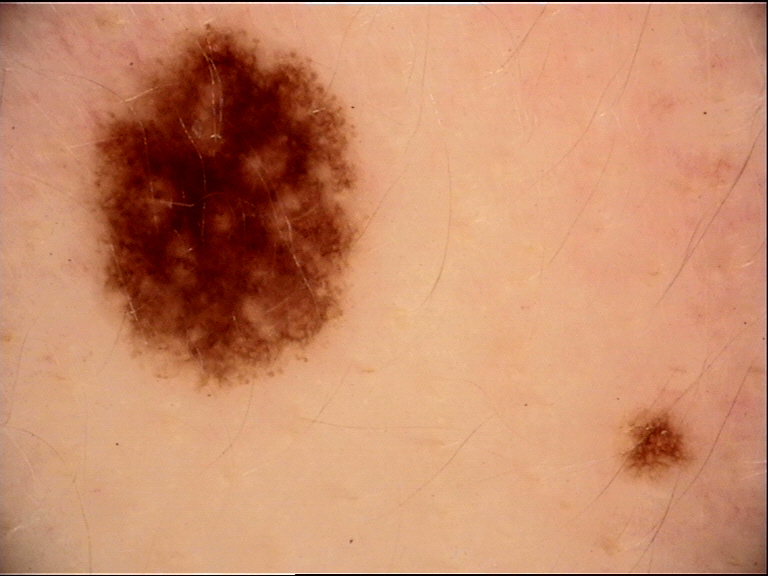Findings:
- image · dermoscopy
- label · dysplastic junctional nevus (expert consensus)